This is a close-up image — 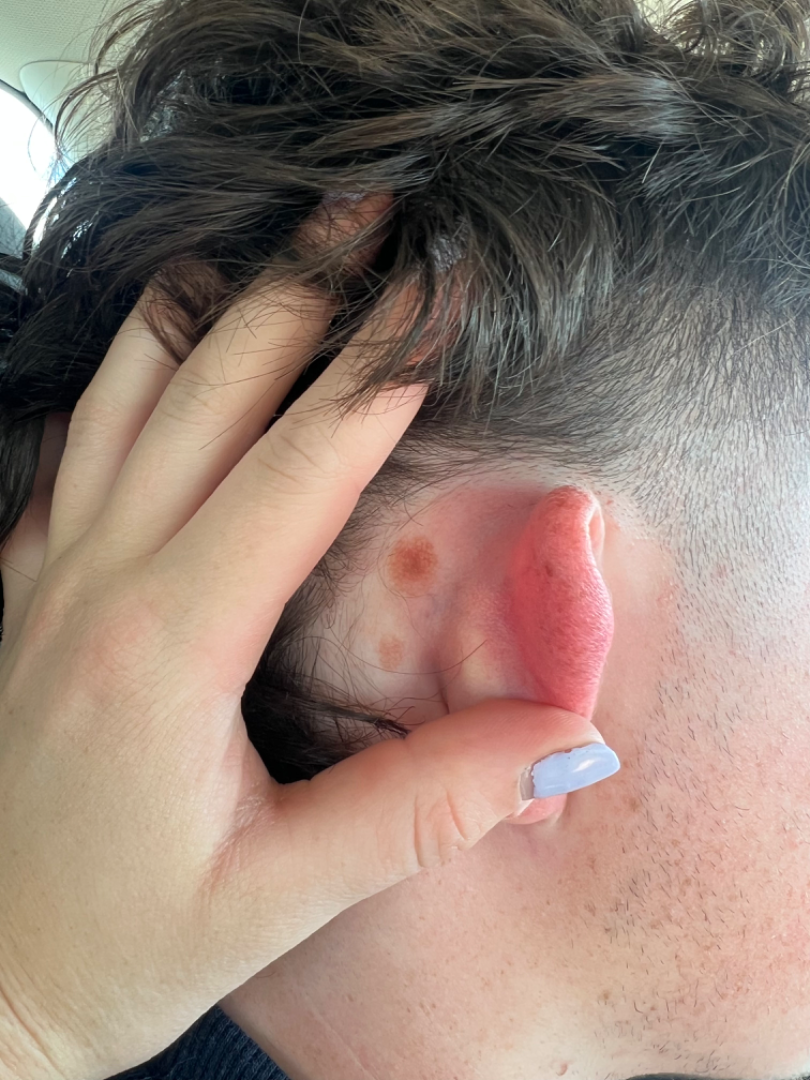{"assessment": "unable to determine"}